A male subject aged 68-72 · dermoscopy of a skin lesion:
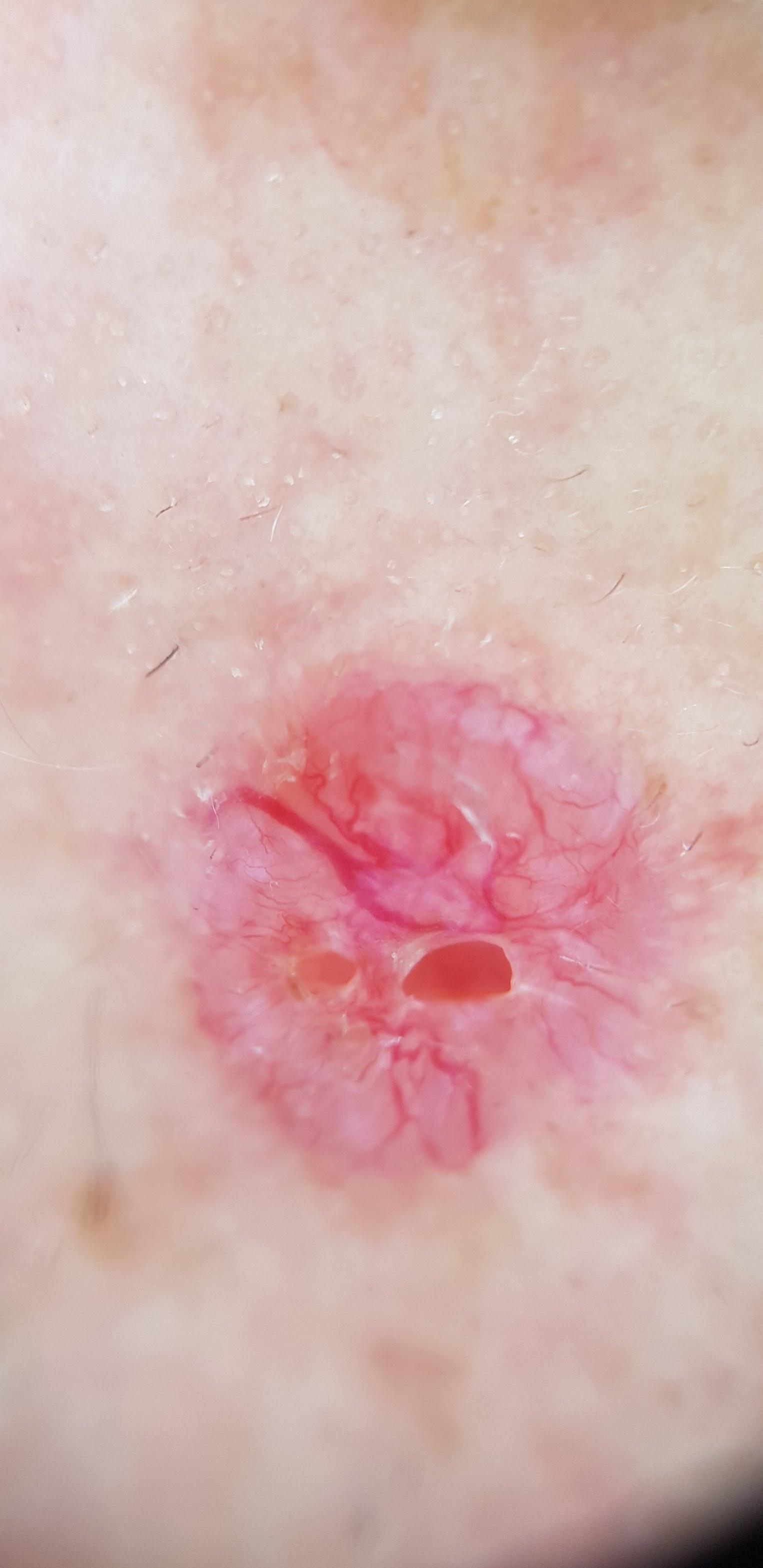Q: Where is the lesion located?
A: the head or neck
Q: What did the workup show?
A: Basal cell carcinoma (biopsy-proven)